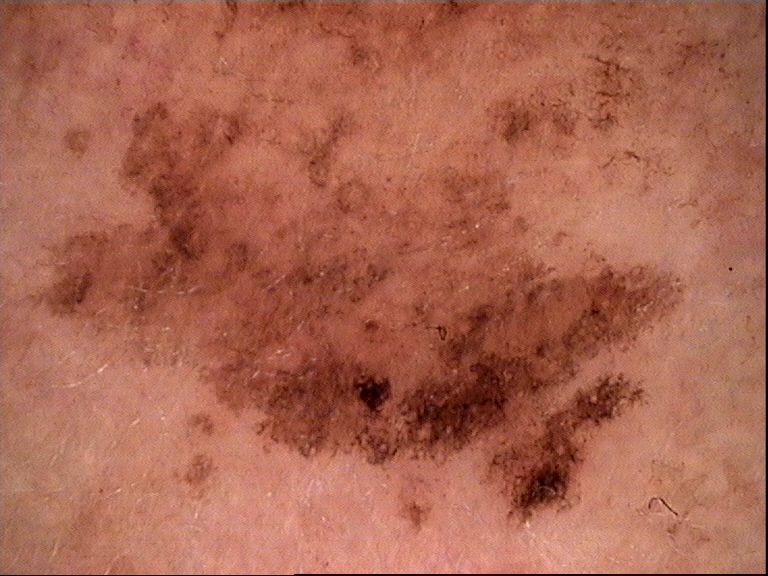Q: What is the diagnosis?
A: solar lentigo (expert consensus)